The patient described the issue as a rash. The photo was captured at an angle. Female subject, age 18–29. The front of the torso, leg, arm, back of the torso and head or neck are involved. The patient indicates the lesion is fluid-filled and raised or bumpy. Symptoms reported: enlargement and itching. Reported duration is less than one week: 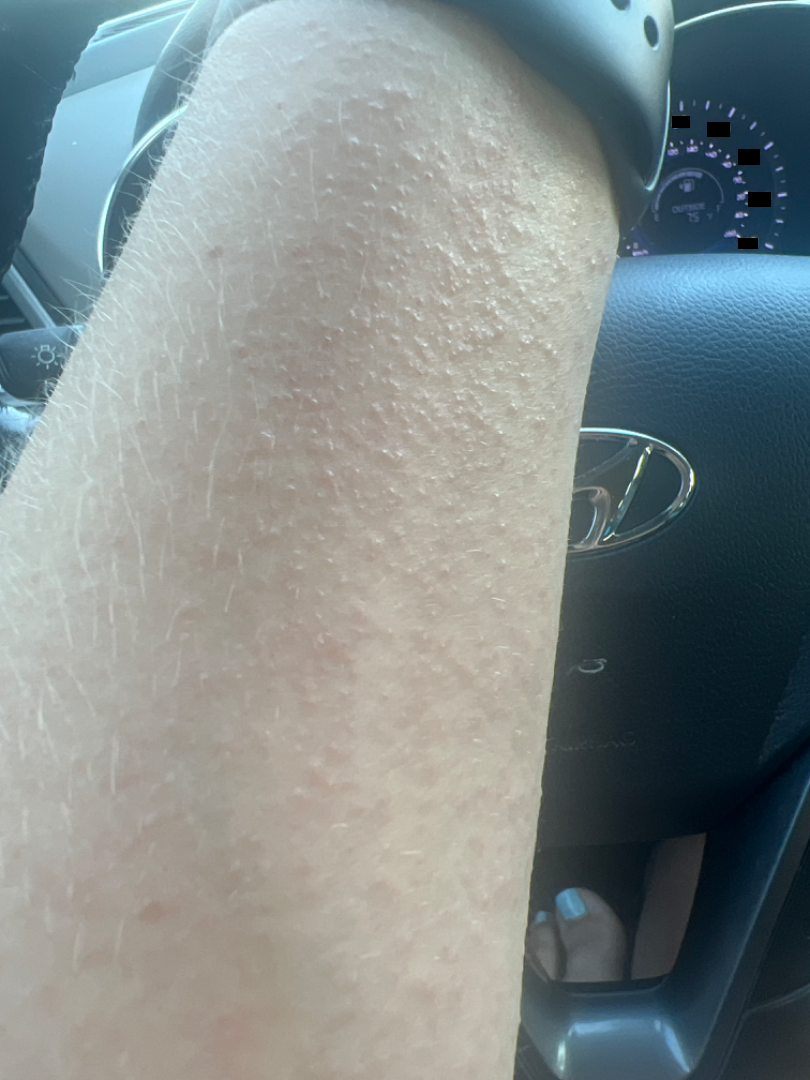Impression: The primary impression is Miliaria; possibly Eczema; also on the differential is Photodermatitis.